A dermoscopy image of a single skin lesion.
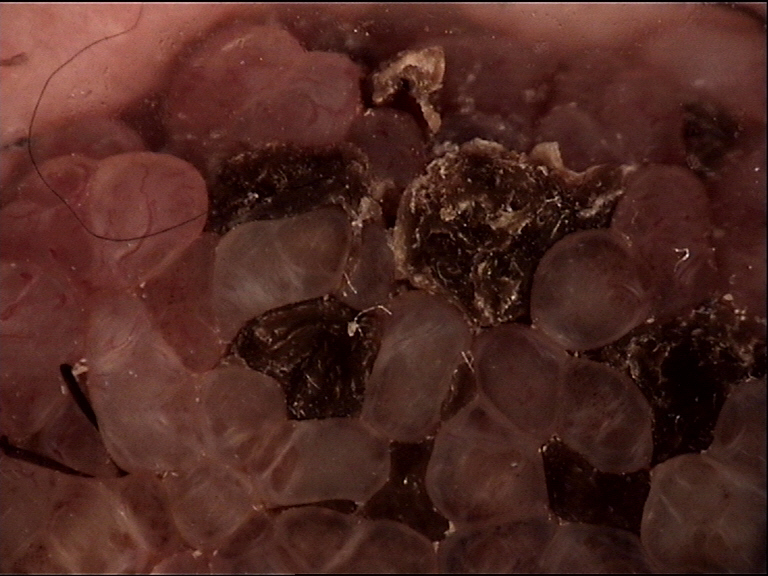- category — banal
- diagnosis — congenital compound nevus (expert consensus)